A clinical photograph showing a skin lesion. A subject age 39 — 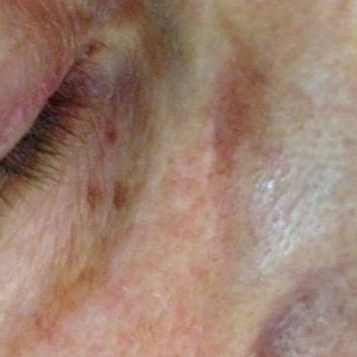Located on the face. The patient reports that the lesion itches, but is not elevated and does not hurt. The diagnostic impression was a lesion of indeterminate malignant potential — an actinic keratosis.